A female patient aged approximately 35, dermoscopy of a skin lesion:
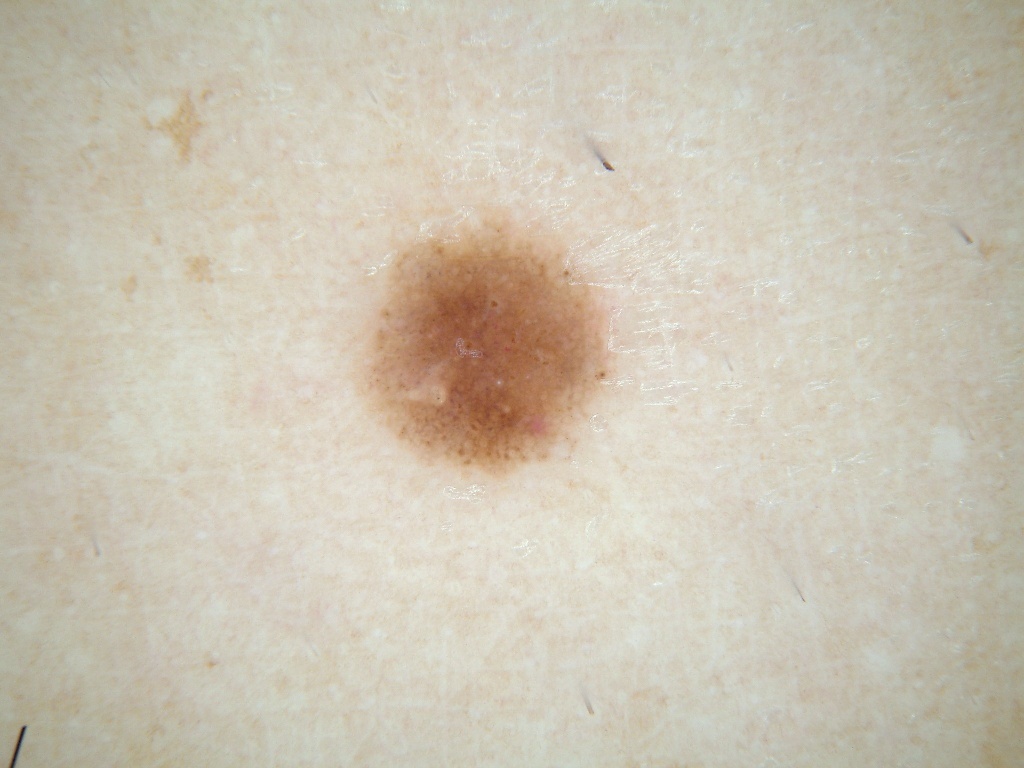lesion location — 359 210 609 475 | features — pigment network and milia-like cysts; absent: globules, negative network, and streaks | diagnostic label — a melanocytic nevus, a benign skin lesion.